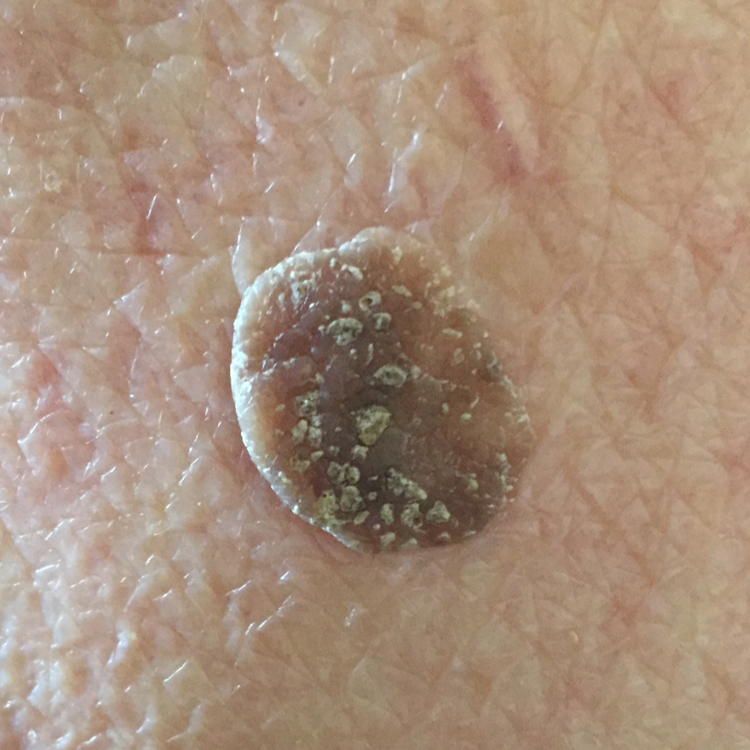patient = female, in their early 90s
image = smartphone clinical photo
skin phototype = I
exposures = prior malignancy (patient or family), prior skin cancer (patient or family), no alcohol use, no tobacco use
region = the back
lesion size = approx. 7 × 4 mm
reported symptoms = elevation, growth / no bleeding, no itching
assessment = seborrheic keratosis (clinical consensus)